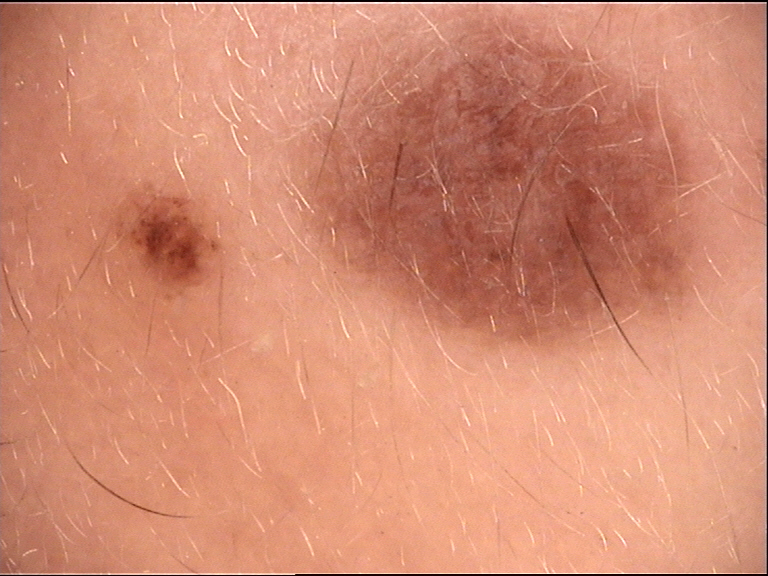modality = dermoscopy | lesion type = banal | class = compound nevus (expert consensus).